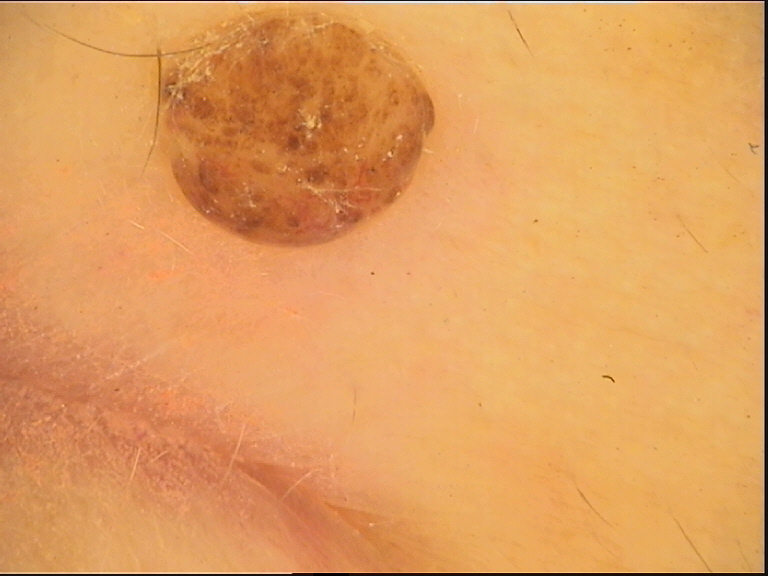A skin lesion imaged with a dermatoscope. Consistent with a banal lesion — a dermal nevus.